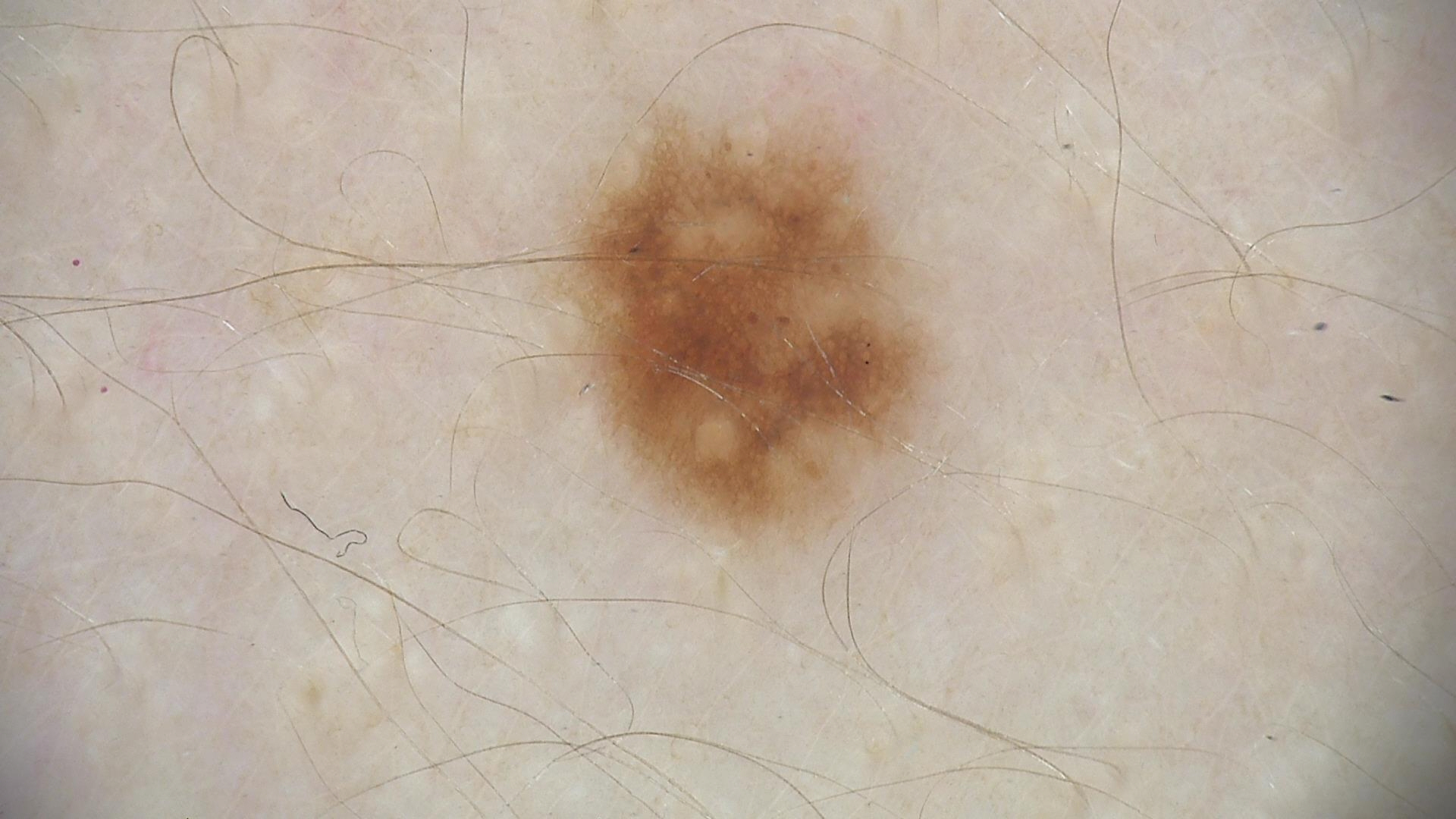imaging = dermoscopy
assessment = dysplastic junctional nevus (expert consensus)